Close-up view: 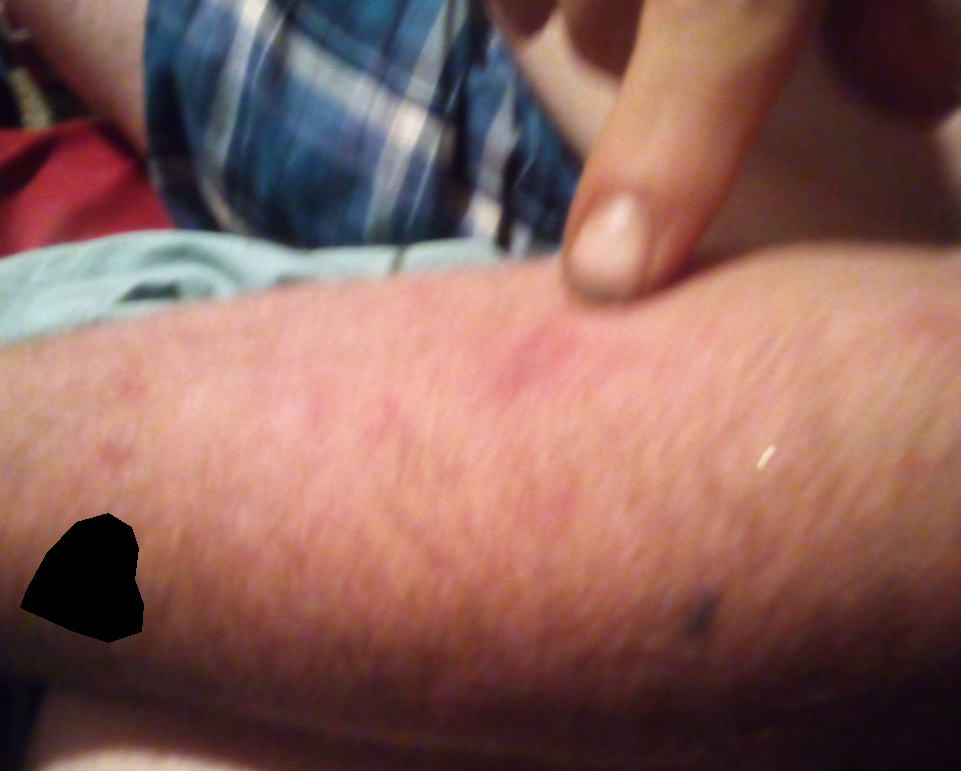Impression: The skin condition could not be confidently assessed from this image.